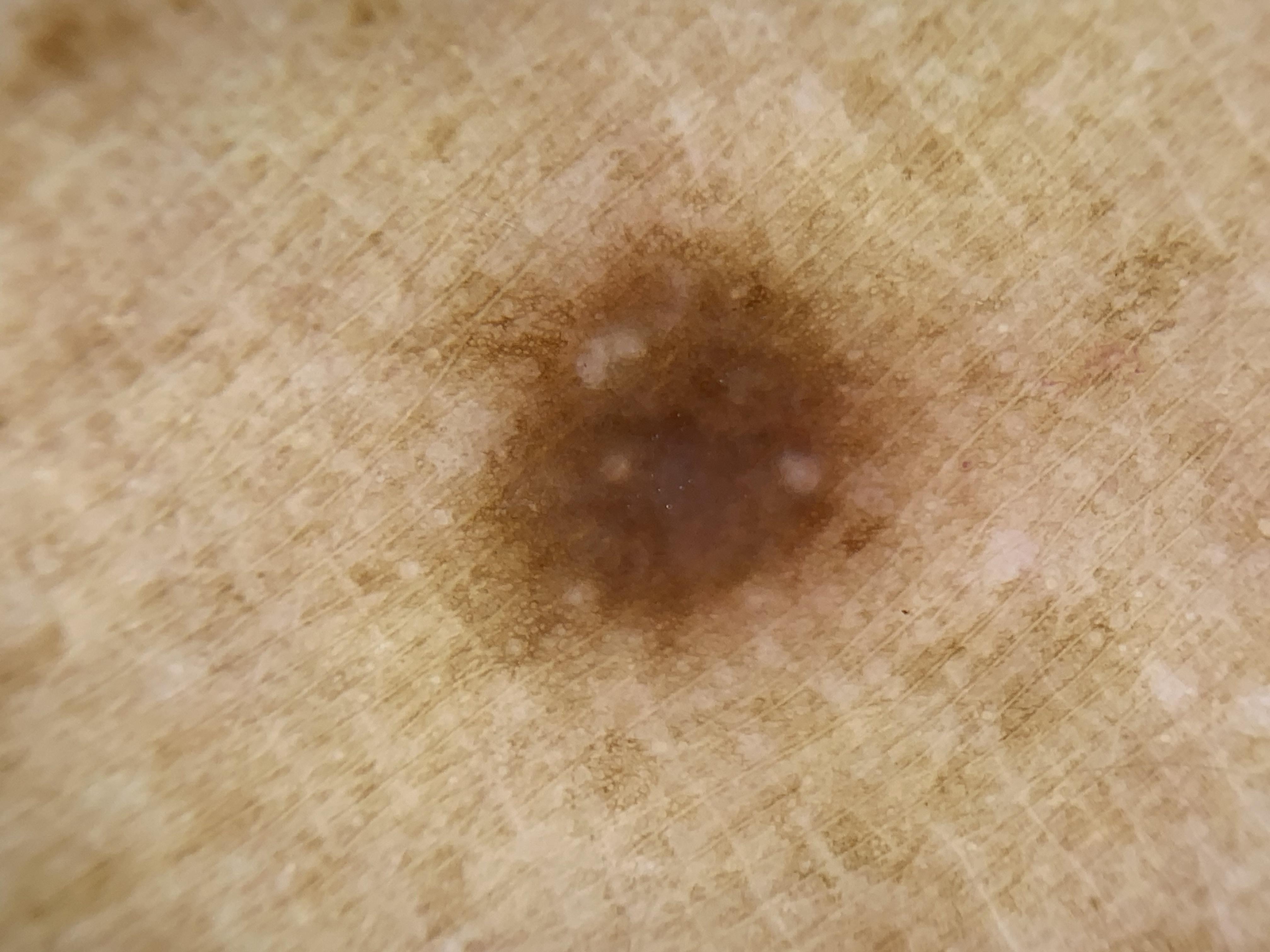Case:
• diagnostic label — Dermatofibroma (biopsy-proven)